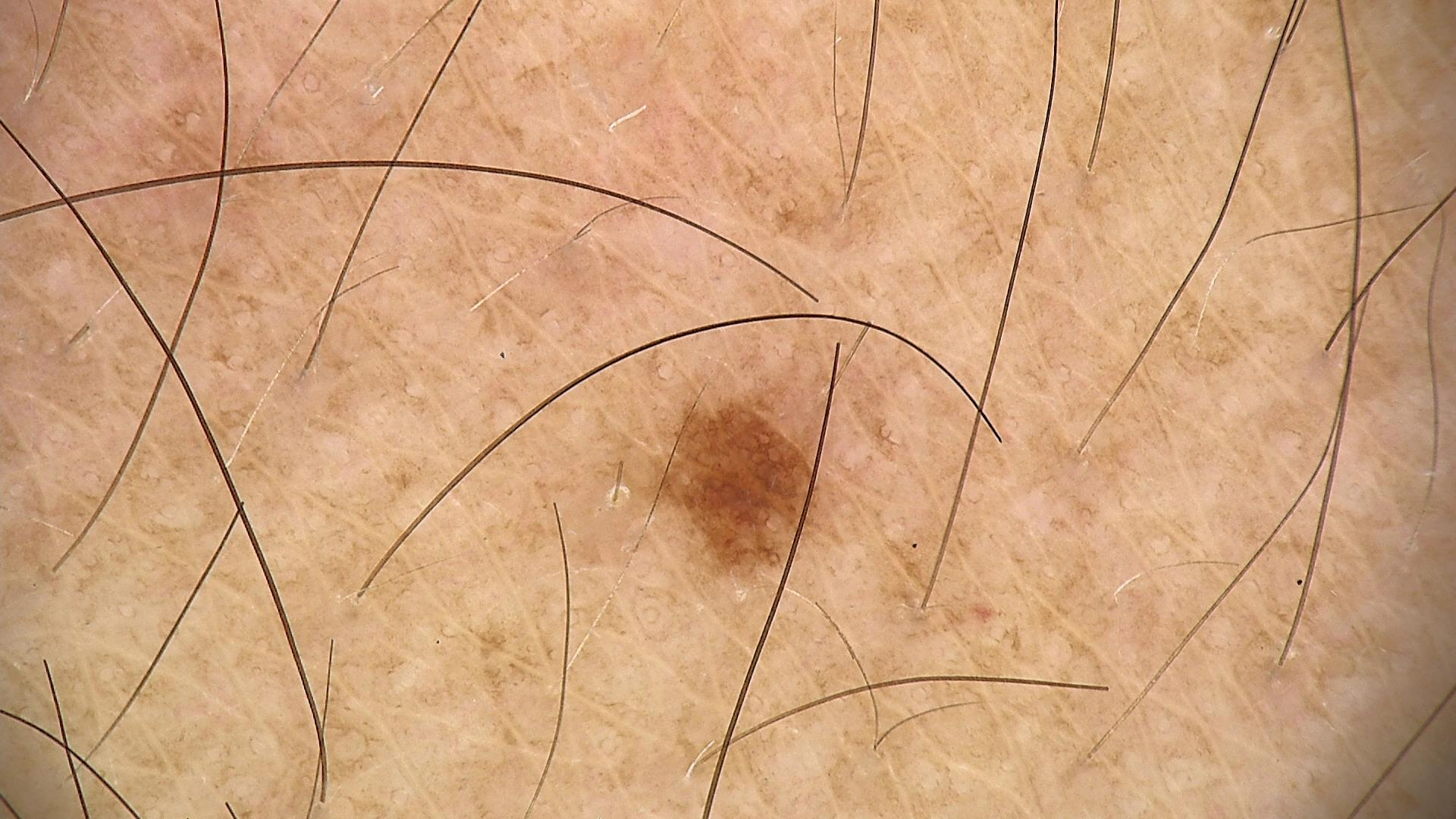Q: What is the imaging modality?
A: dermatoscopy
Q: What was the diagnostic impression?
A: dysplastic junctional nevus (expert consensus)